The contributor is 18–29, male. The leg is involved. The photo was captured at a distance.
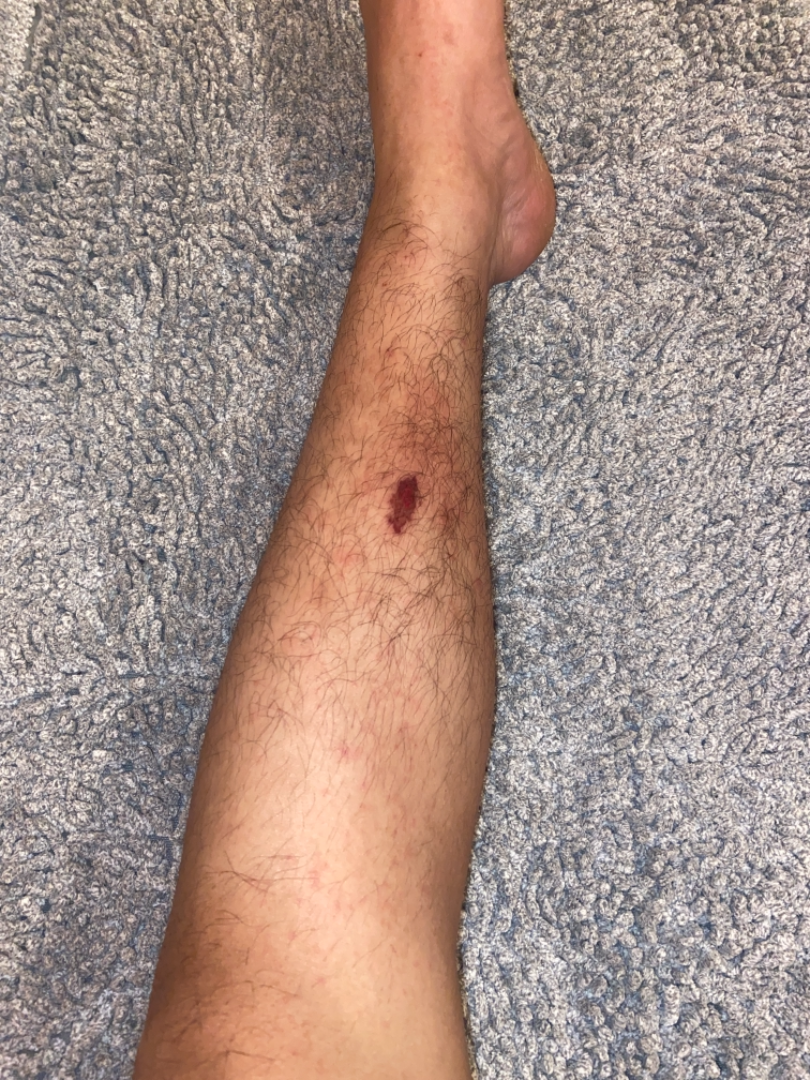The reviewing dermatologist was unable to assign a differential diagnosis from the image.